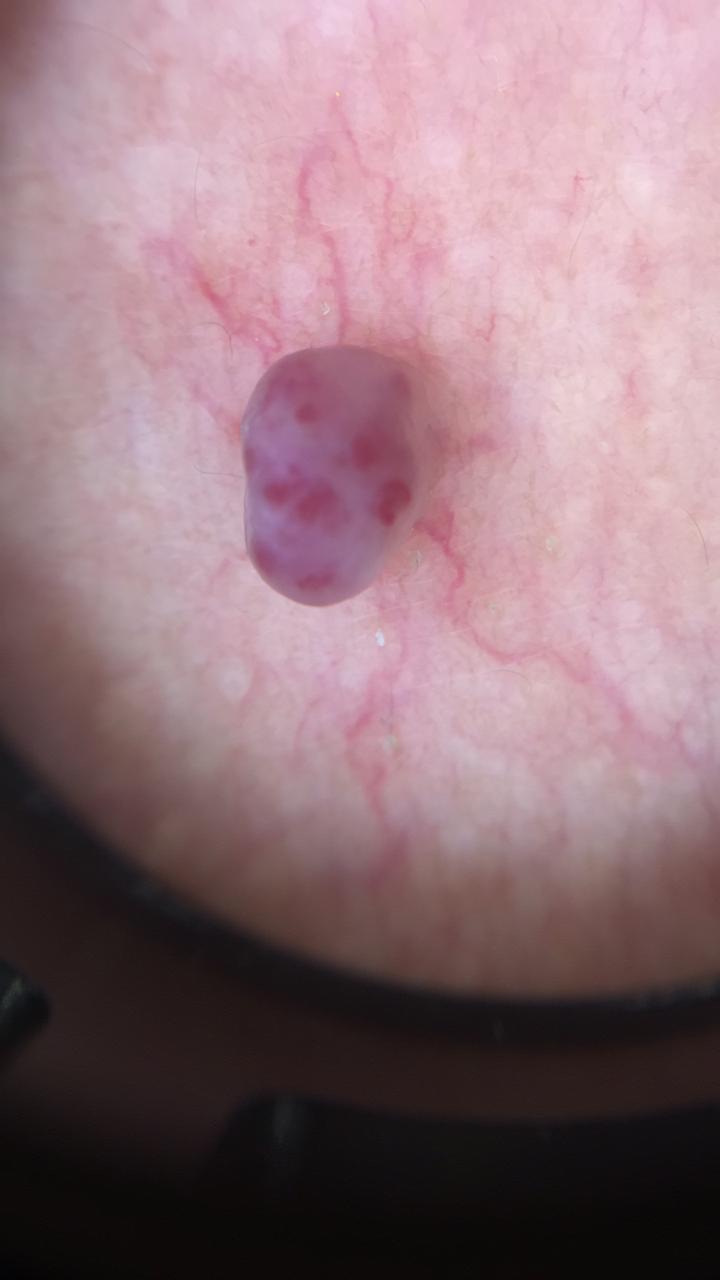image = dermatoscopic image | skin phototype = III | patient = male, aged 43 to 47 | site = the trunk | pathology = vascular lesion (biopsy-proven).